An image taken at a distance:
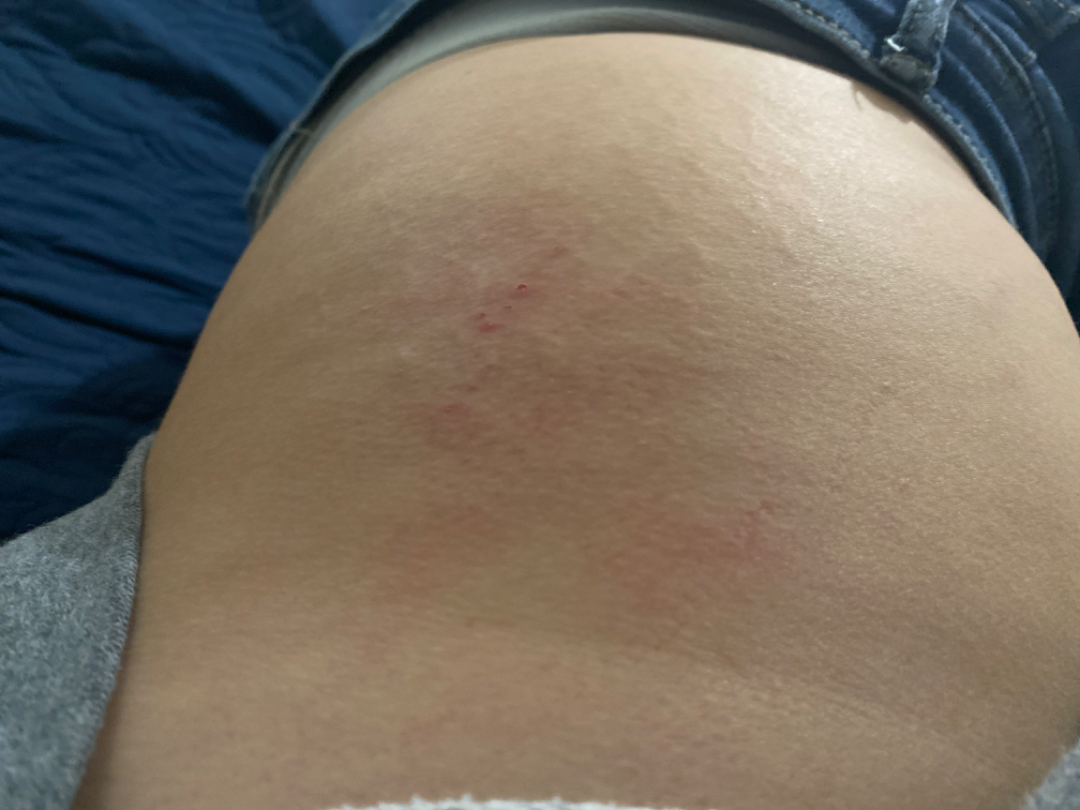  texture: raised or bumpy
  symptoms:
    - itching
    - bleeding
  patient_category: a rash
  systemic_symptoms: none reported
  differential:
    leading:
      - Eczema
    considered:
      - Contact dermatitis, NOS
    unlikely:
      - Urticaria